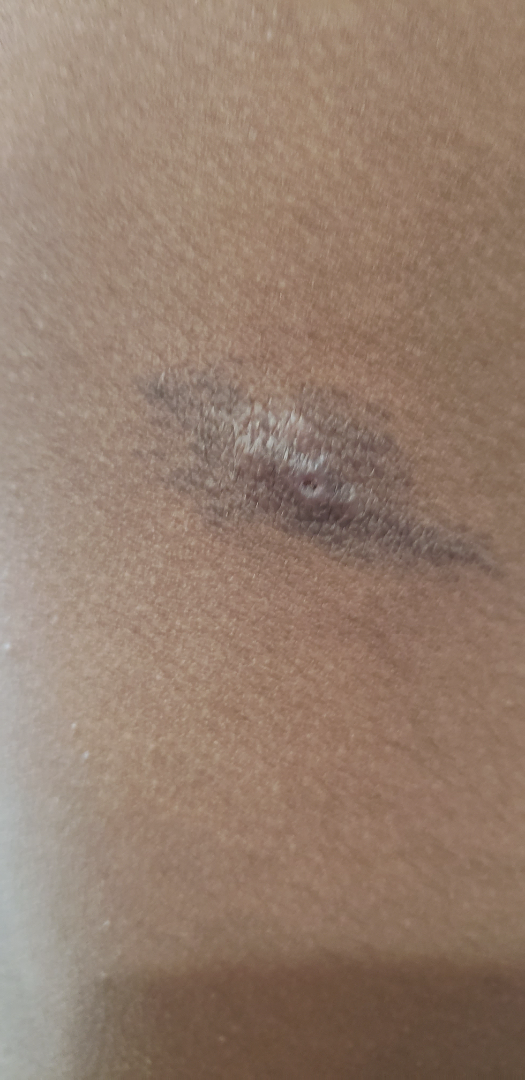Close-up view. A single dermatologist reviewed the case: Abscess, Cyst and Hidradenitis were considered with similar weight.